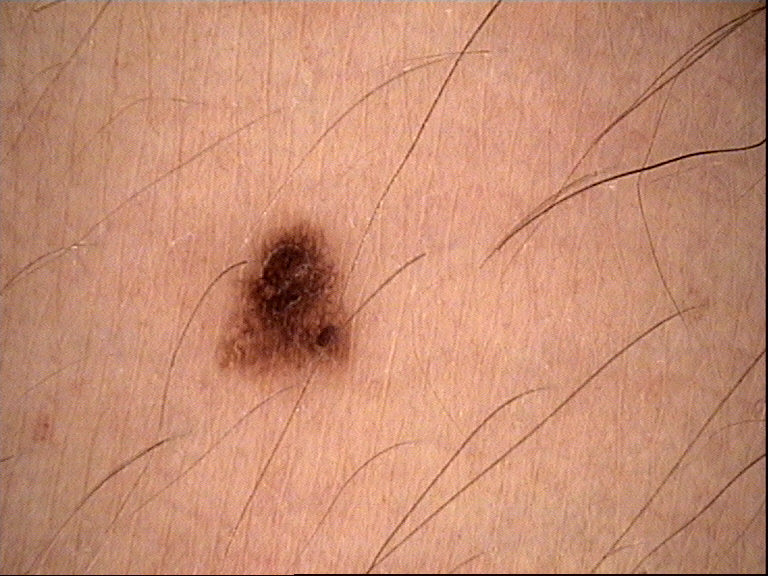assessment=dysplastic junctional nevus (expert consensus).